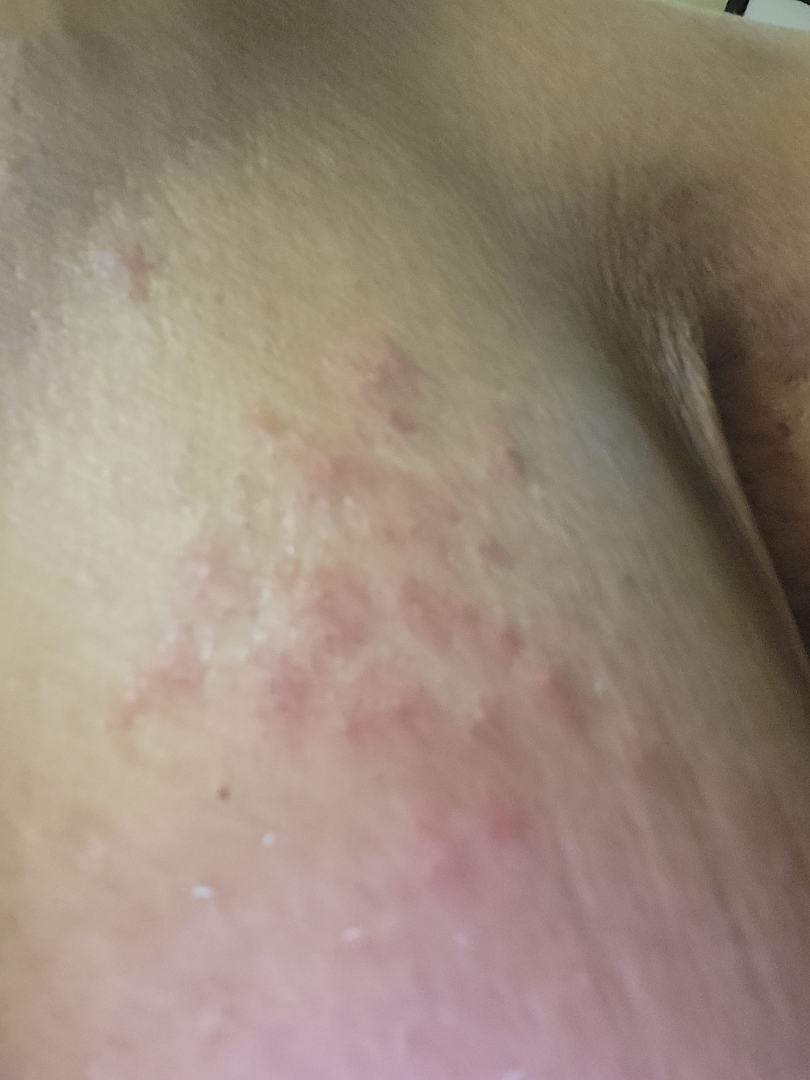| field | value |
|---|---|
| assessment | unable to determine |